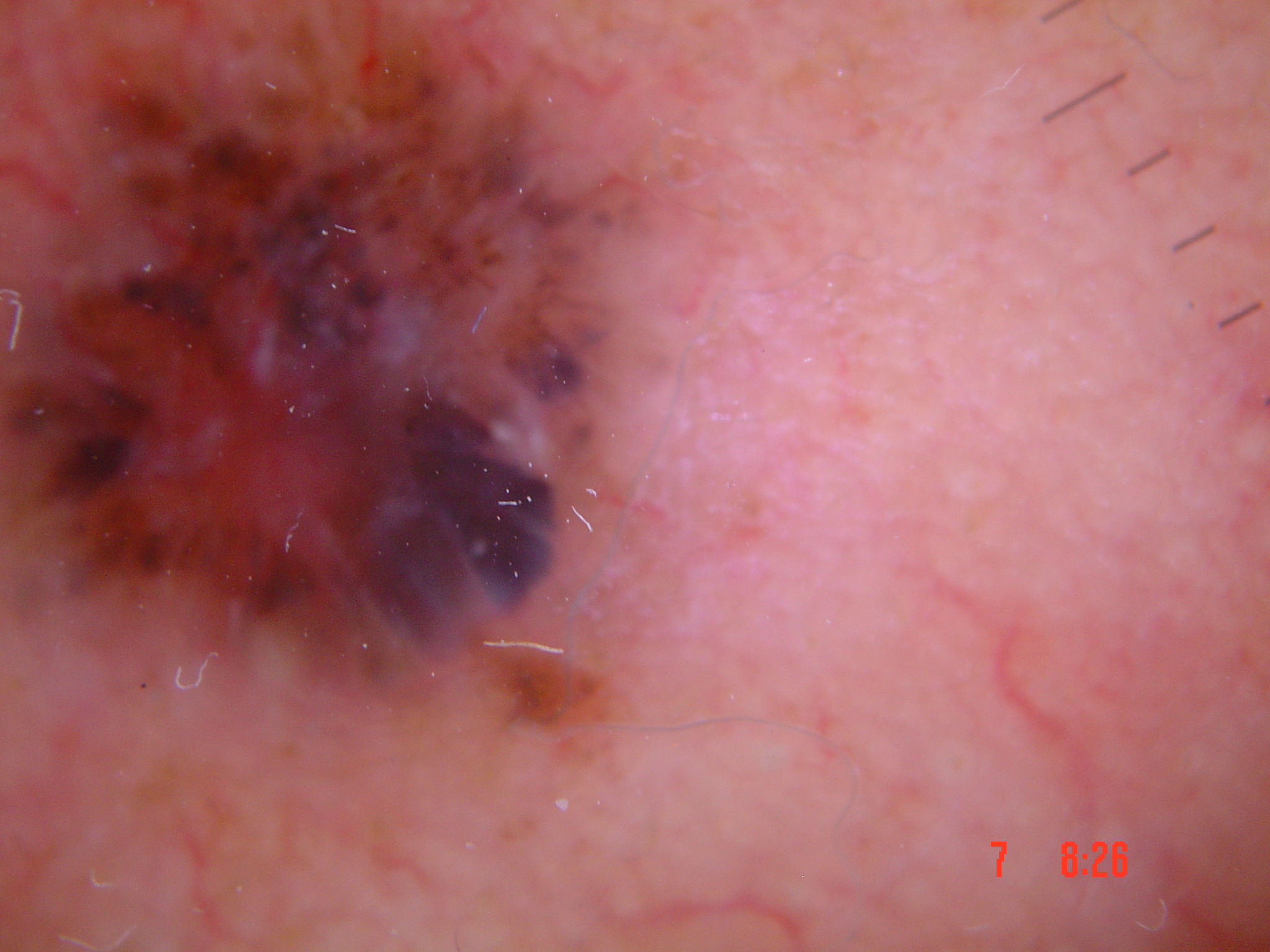{"diagnosis": {"name": "basal cell carcinoma", "code": "bcc", "malignancy": "malignant", "super_class": "non-melanocytic", "confirmation": "histopathology"}}